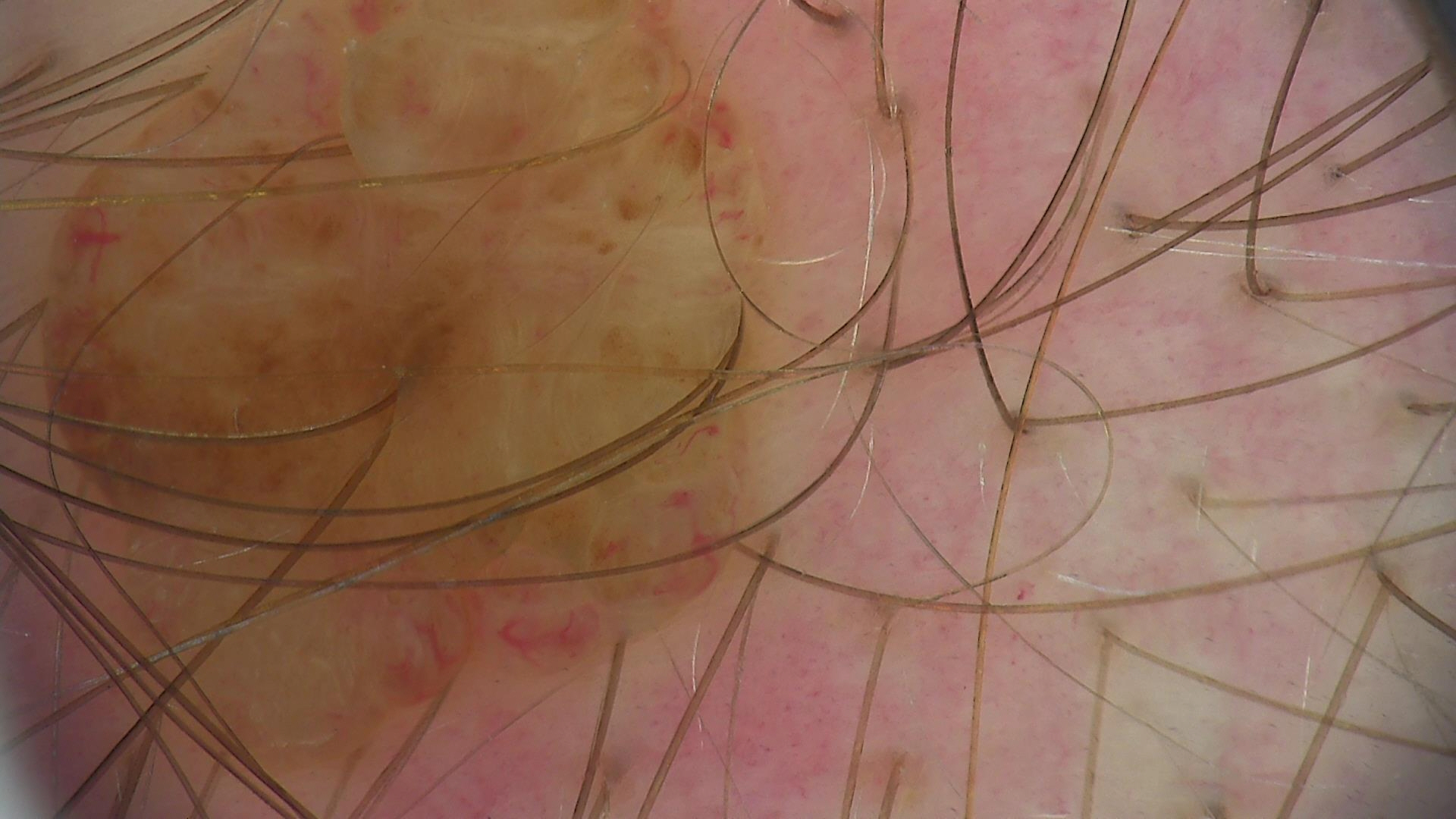A skin lesion imaged with a dermatoscope.
The morphology is that of a banal lesion.
The diagnostic label was a dermal nevus.